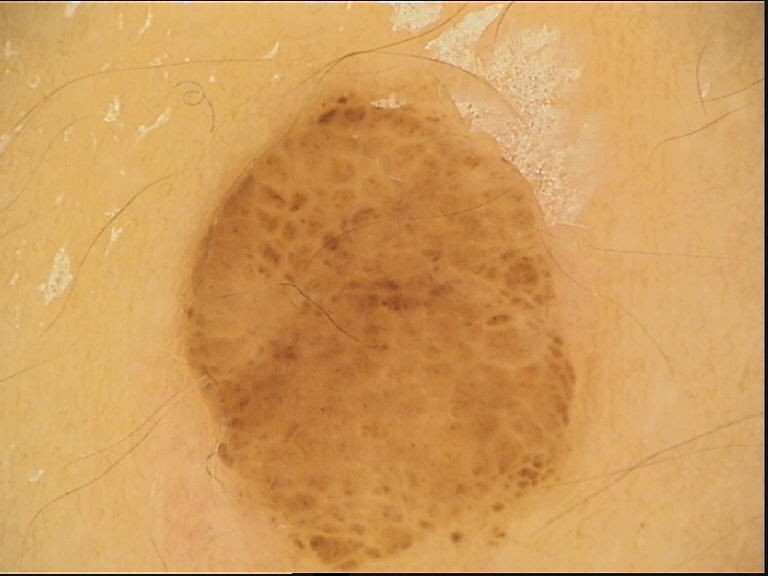| key | value |
|---|---|
| image | dermatoscopy |
| classification | banal |
| class | dermal nevus (expert consensus) |